A male subject, roughly 70 years of age. A dermoscopic image of a skin lesion — 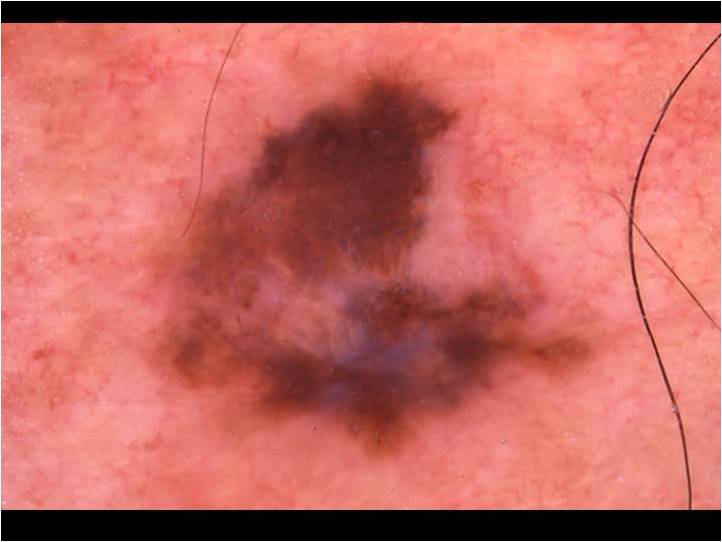Summary:
On dermoscopy, the lesion shows no milia-like cysts, streaks, globules, negative network, or pigment network. The lesion occupies the region <bbox>127, 61, 595, 463</bbox>.
Conclusion:
Histopathologically confirmed as a melanoma, a skin cancer.